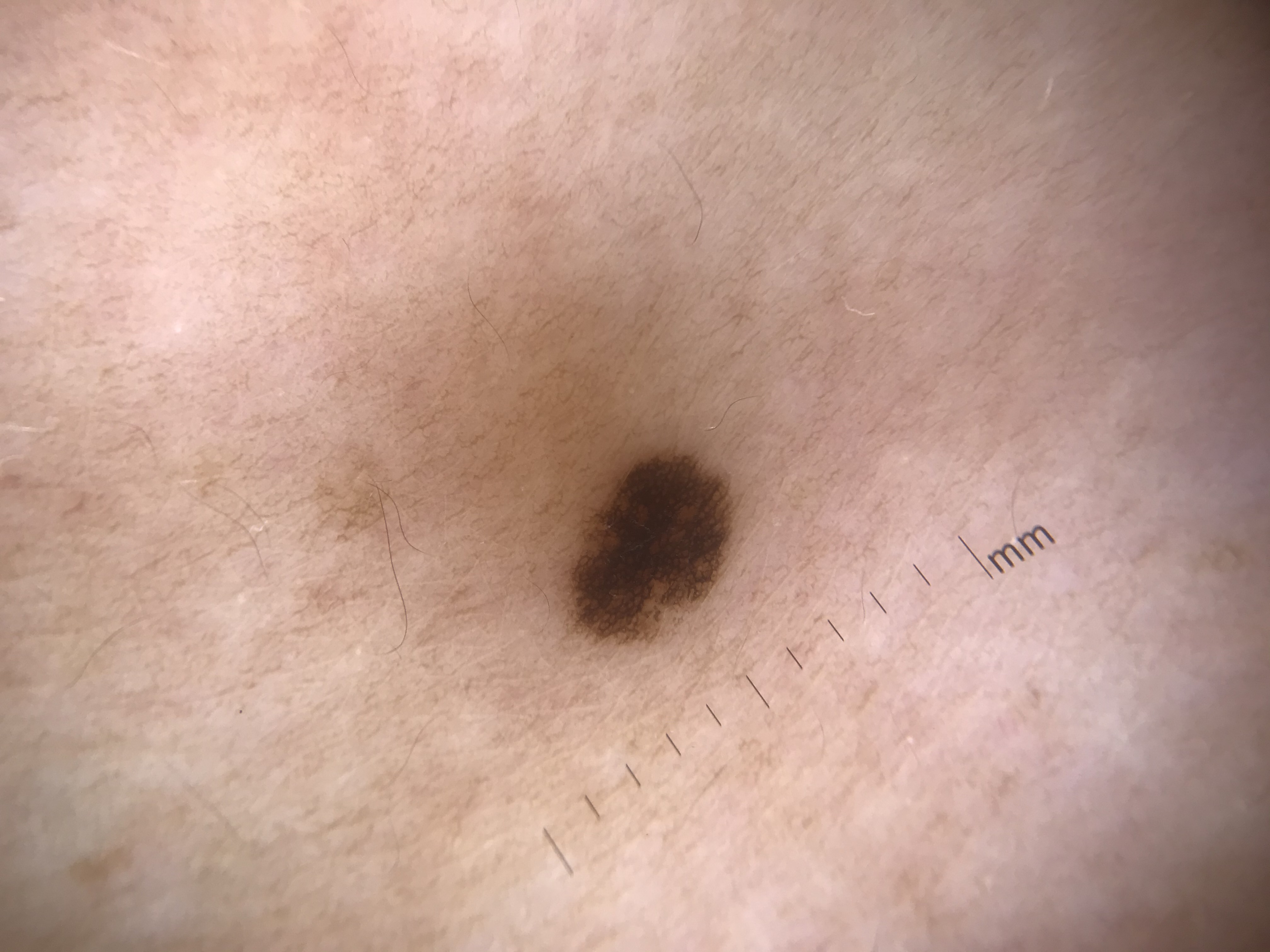A dermoscopy image of a single skin lesion. This is a banal lesion. The diagnosis was a junctional nevus.